A dermatoscopic image of a skin lesion.
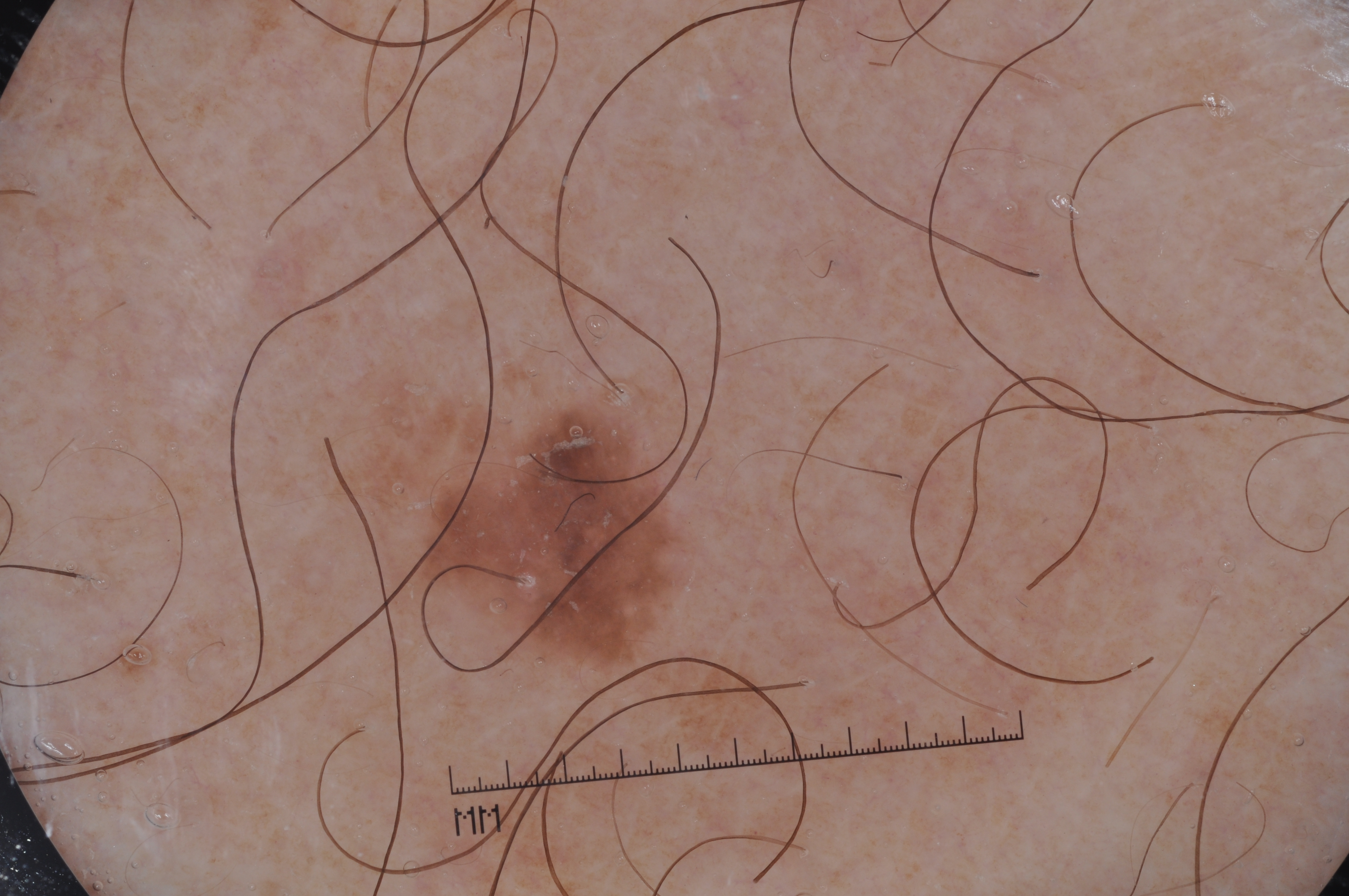<lesion>
<lesion_location>
  <bbox_xyxy>281, 327, 750, 717</bbox_xyxy>
</lesion_location>
<diagnosis>
  <name>seborrheic keratosis</name>
  <malignancy>benign</malignancy>
  <lineage>keratinocytic</lineage>
  <provenance>clinical</provenance>
</diagnosis>
</lesion>